Close-up view; the contributor is 18–29, male; located on the arm — 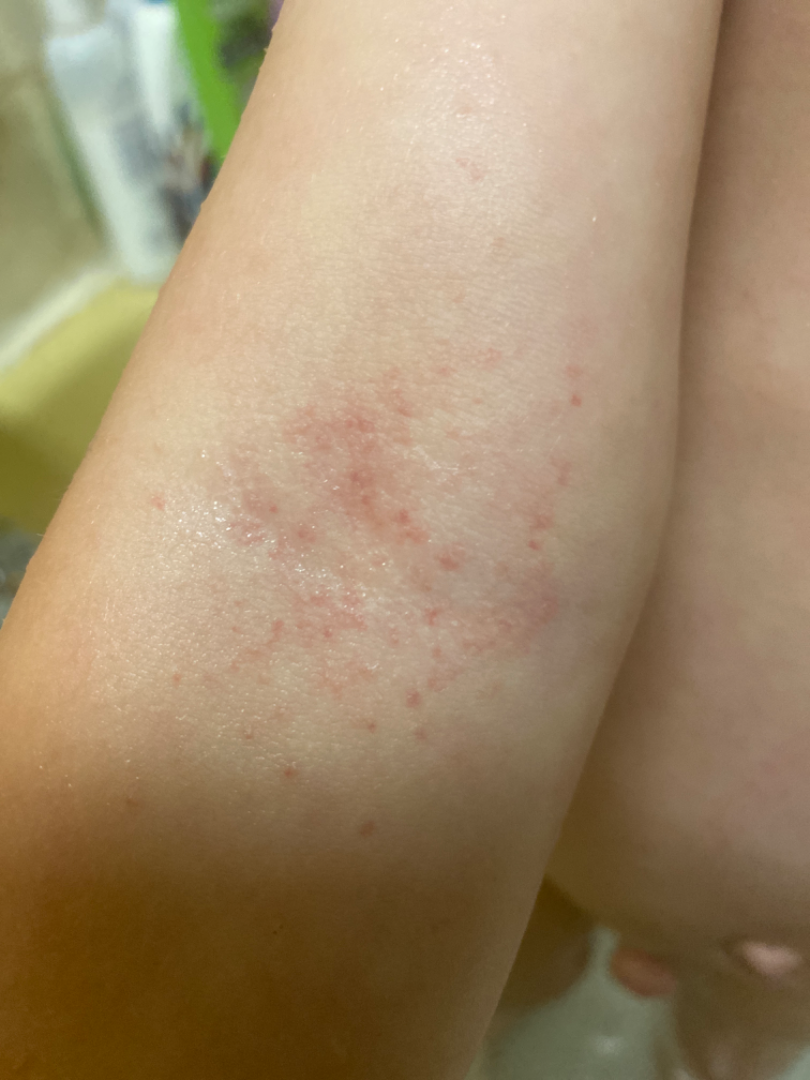{"texture": "flat", "duration": "about one day", "differential": "Eczema"}